This image was taken at an angle · the leg is involved:
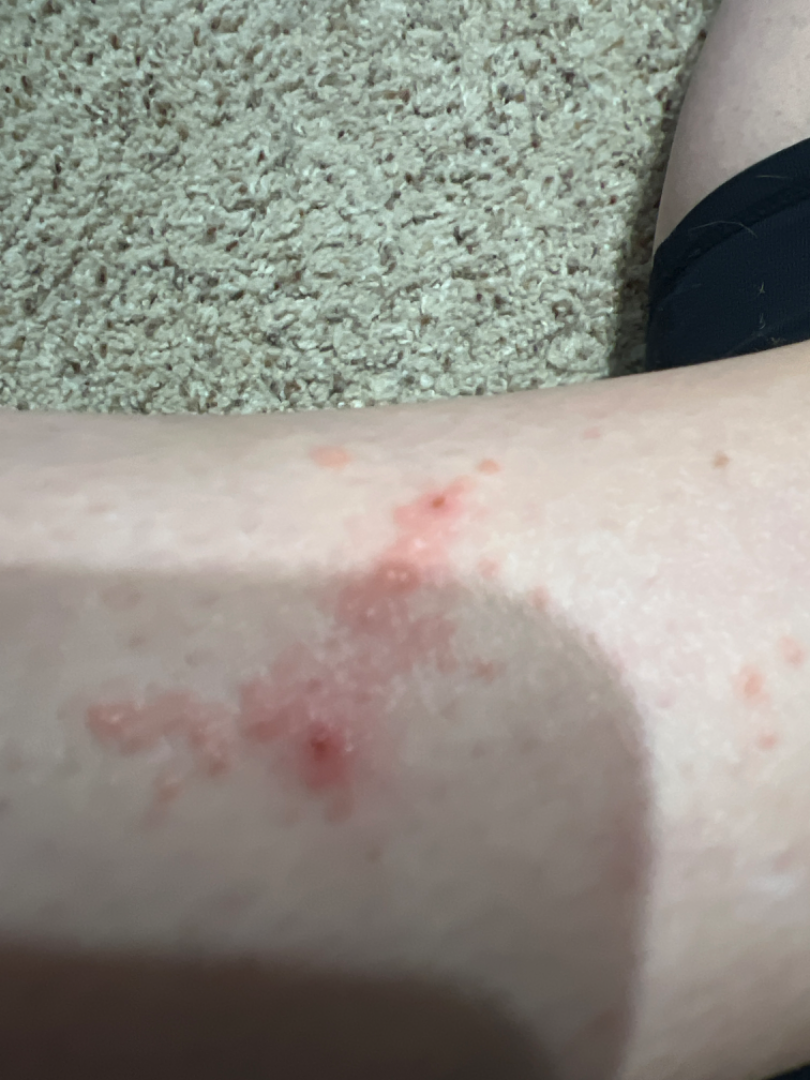On photographic review: the differential includes Cutaneous larva migrans and Allergic Contact Dermatitis, with no clear leading consideration; less probable is Localized skin infection.